The contributor reports the lesion is raised or bumpy; reported lesion symptoms include itching; the subject is a female aged 40–49; the condition has been present for less than one week; close-up view; located on the head or neck — 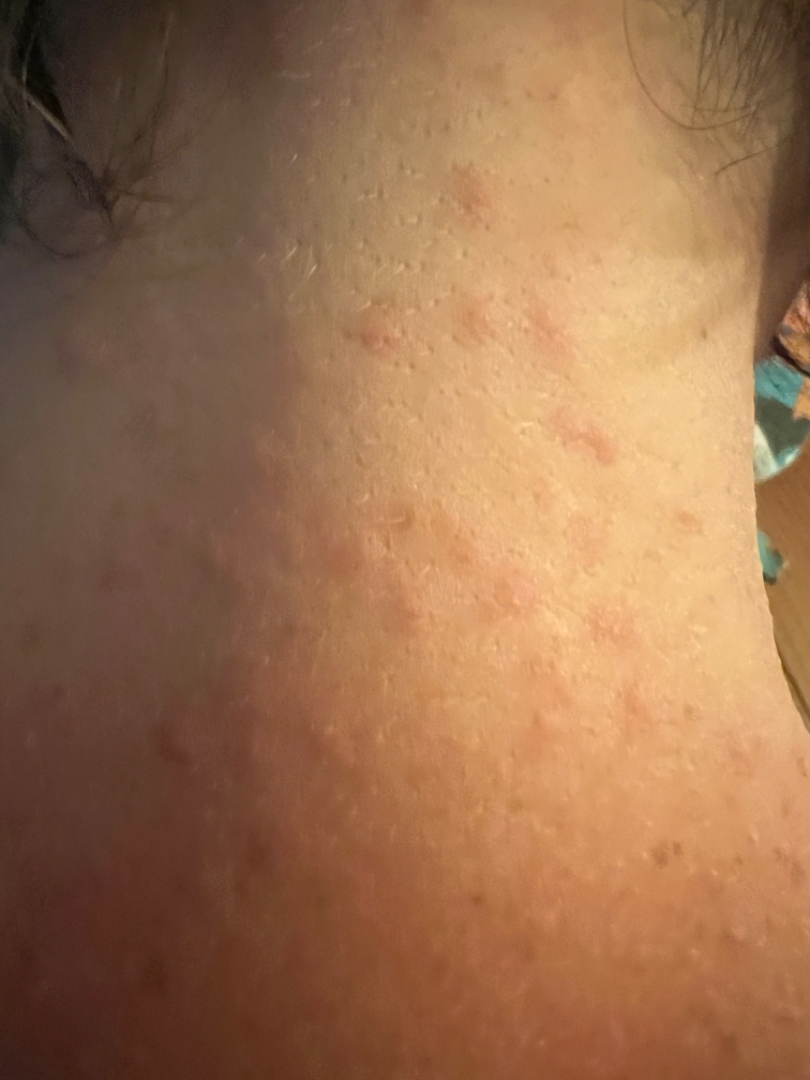Notes:
• differential diagnosis · Folliculitis (considered); Insect Bite (considered)